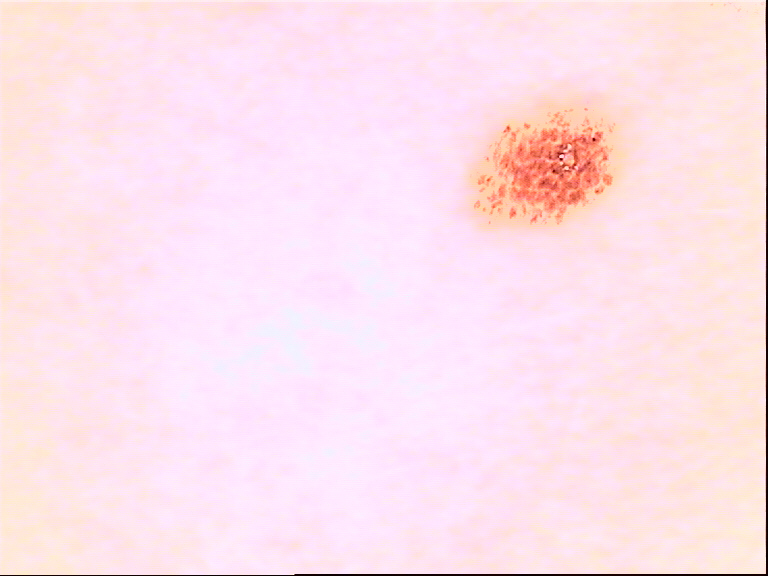Findings:
A dermoscopy image of a single skin lesion.
Conclusion:
The diagnosis was a dysplastic compound nevus.